Dermoscopy of a skin lesion:
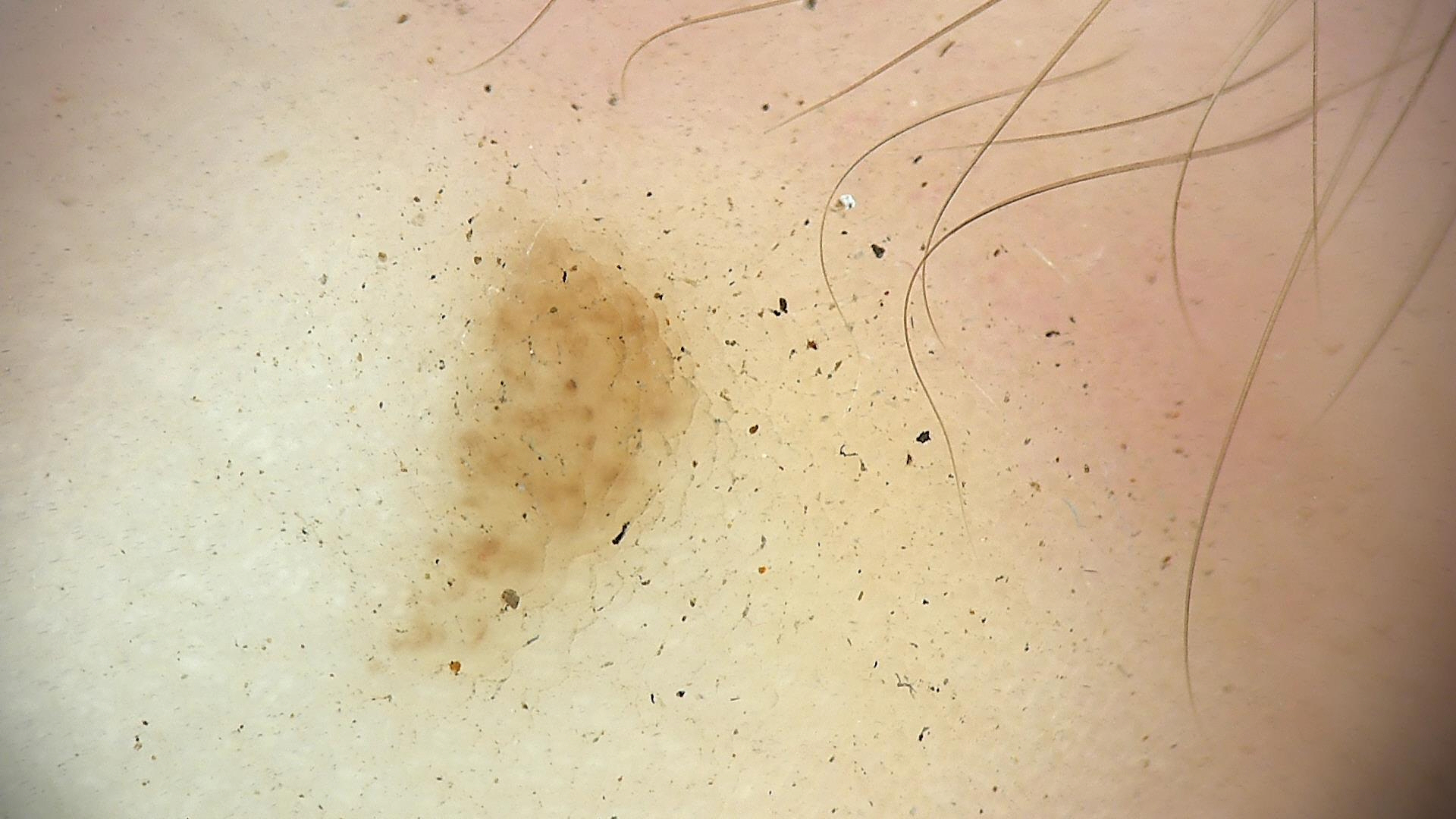• diagnostic label — acral dysplastic junctional nevus (expert consensus)